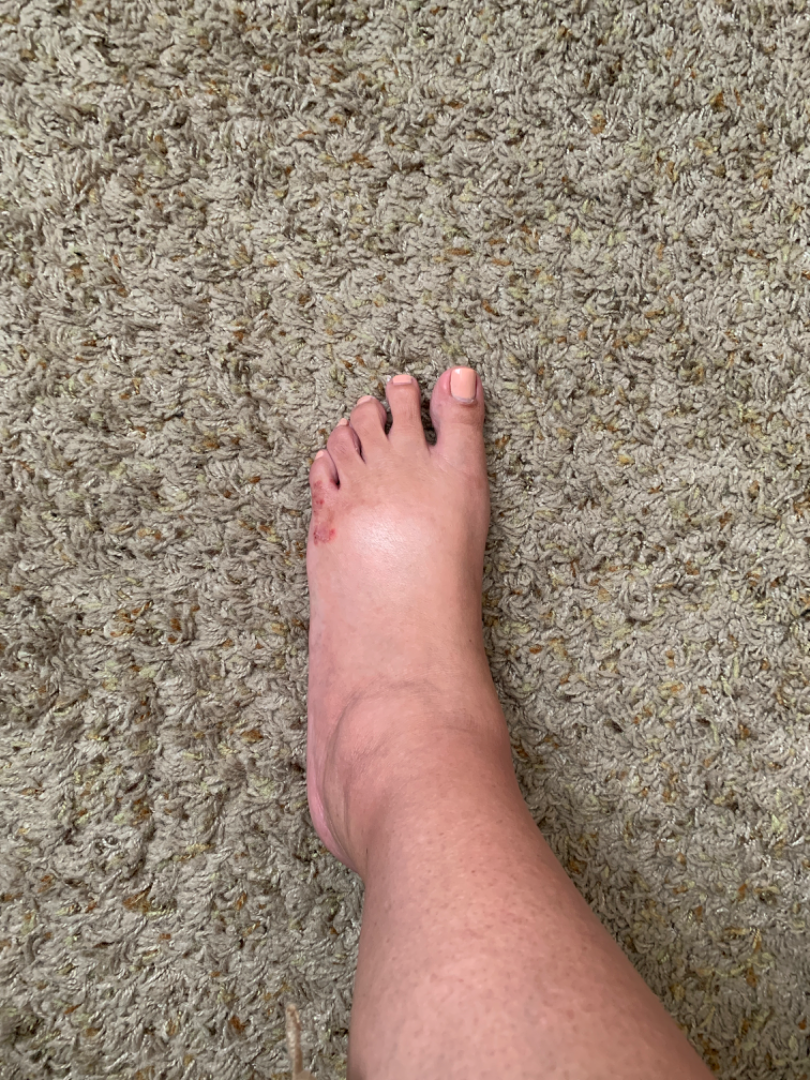The photograph was taken at a distance.
Eczema and Allergic Contact Dermatitis were considered with similar weight.